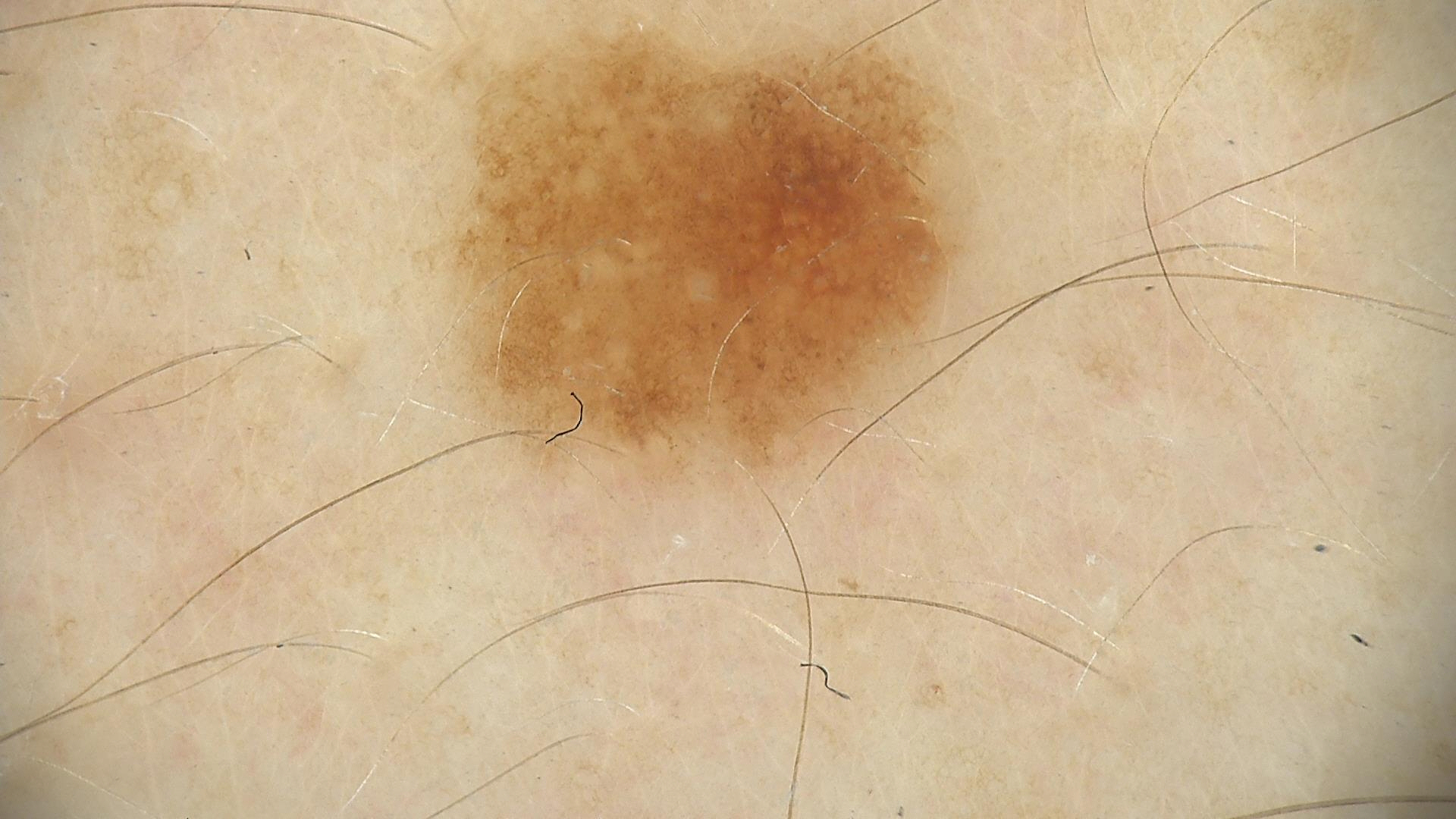modality: dermoscopy; diagnosis: dysplastic junctional nevus (expert consensus).